Located on the arm and head or neck; the contributor is a female aged 30–39; the patient notes burning, bothersome appearance, pain, itching, darkening and enlargement; close-up view: 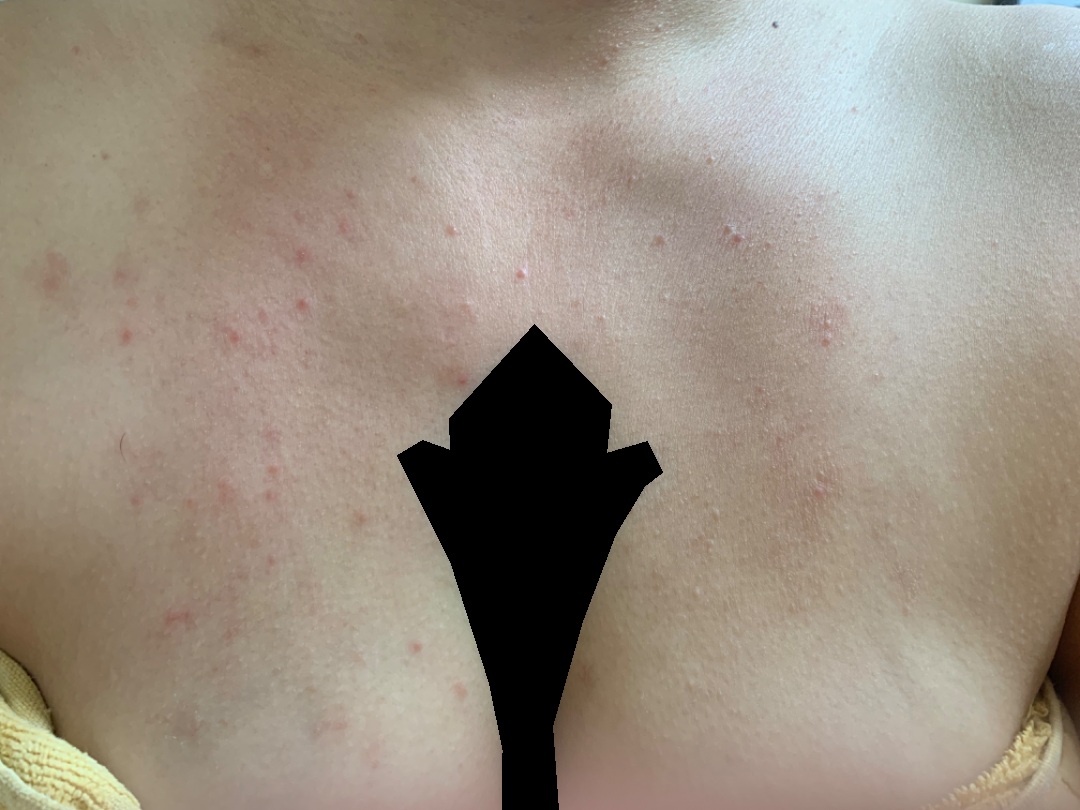Impression:
One reviewing dermatologist: most likely Allergic Contact Dermatitis; possibly Photodermatitis; with consideration of Folliculitis.